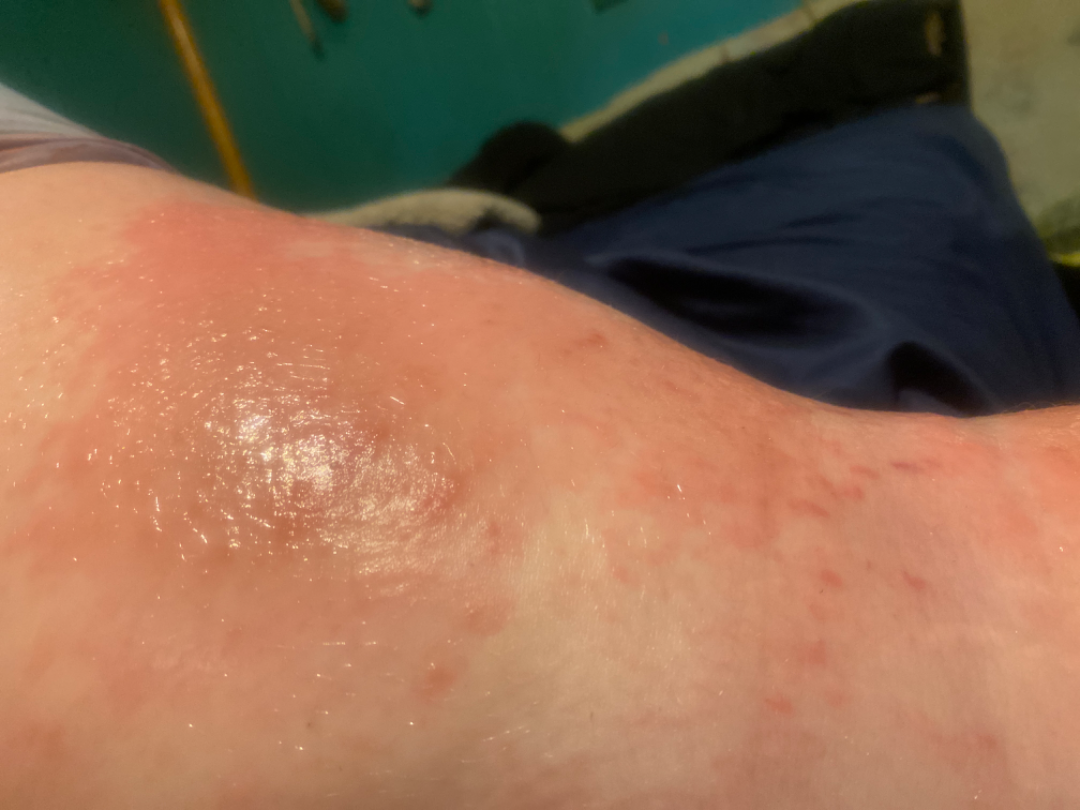Findings:
- site: leg
- patient: female, age 30–39
- shot type: at an angle
- dermatologist impression: the leading consideration is Allergic Contact Dermatitis